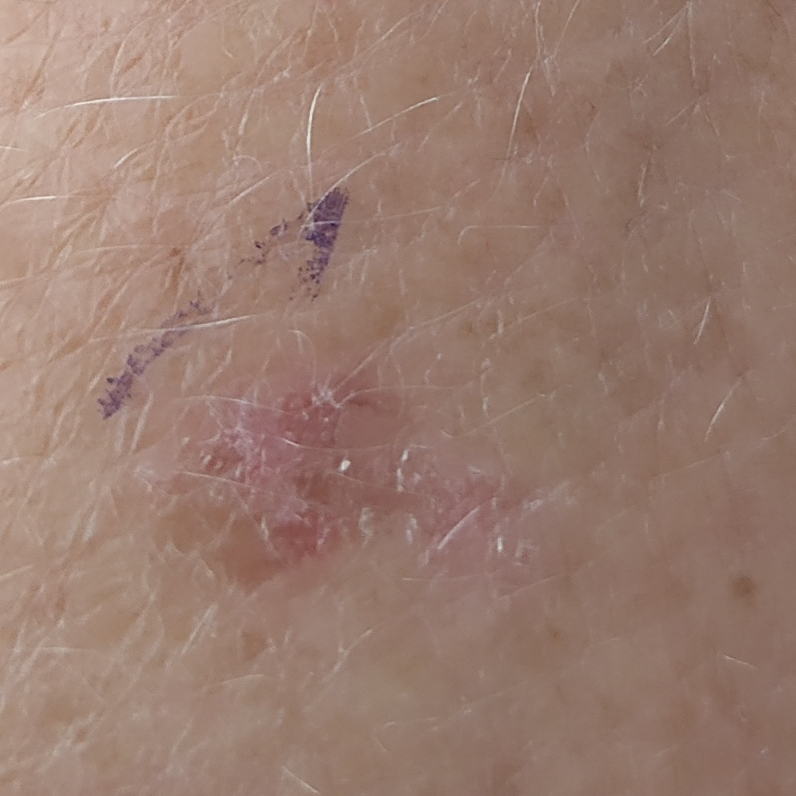A clinical close-up photograph of a skin lesion. A patient 58 years old. The lesion is on a forearm. The patient describes that the lesion itches, but has not changed and has not grown. The diagnostic impression was an actinic keratosis.